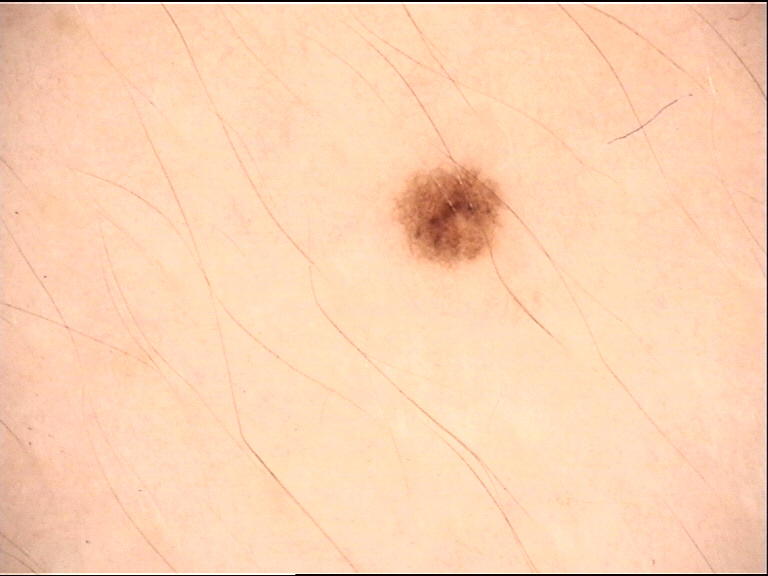{
  "diagnosis": {
    "name": "dysplastic junctional nevus",
    "code": "jd",
    "malignancy": "benign",
    "super_class": "melanocytic",
    "confirmation": "expert consensus"
  }
}